A dermatoscopic image of a skin lesion.
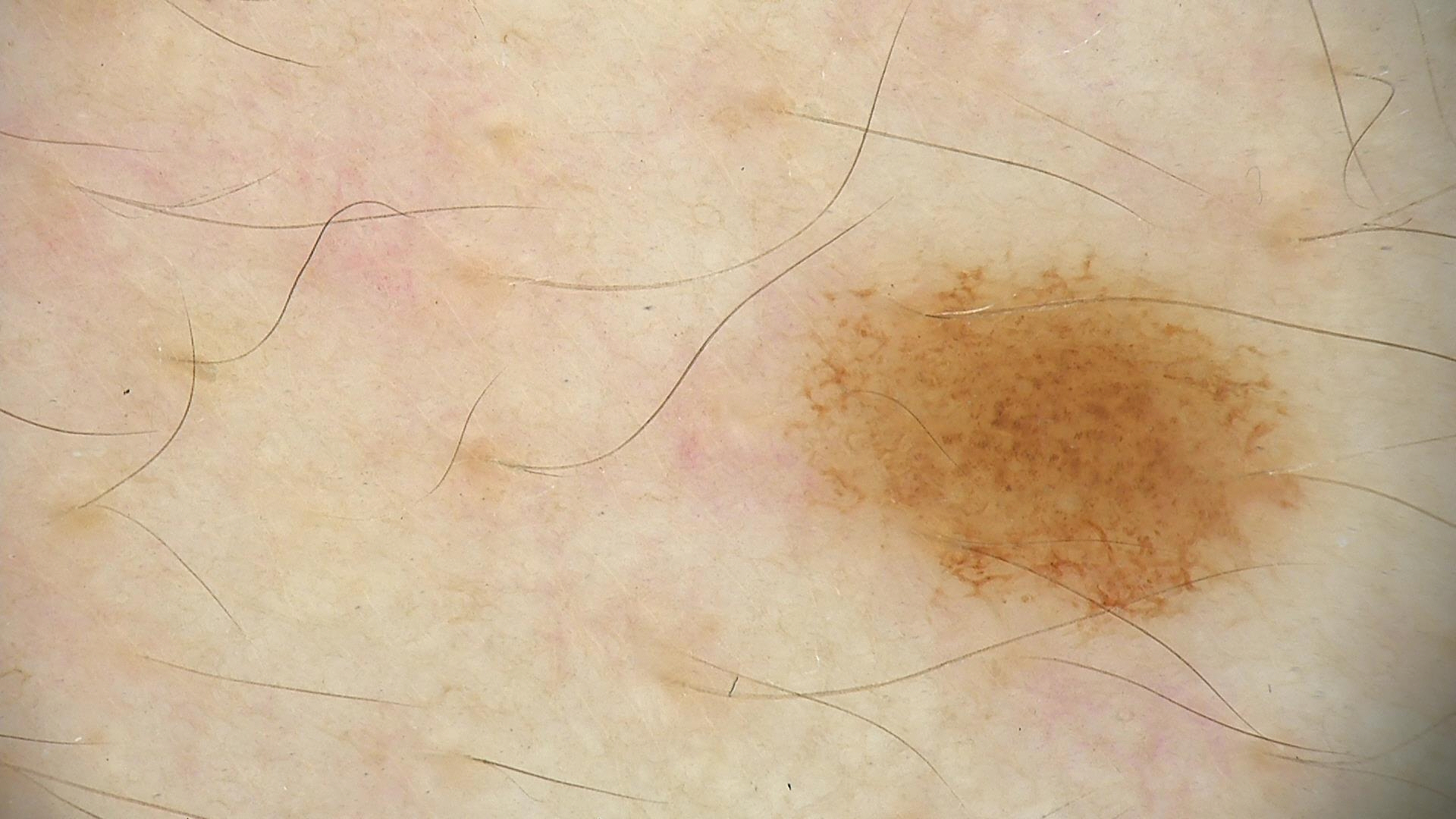Classified as a dysplastic junctional nevus.